Female subject, age 40–49; the photograph is a close-up of the affected area — 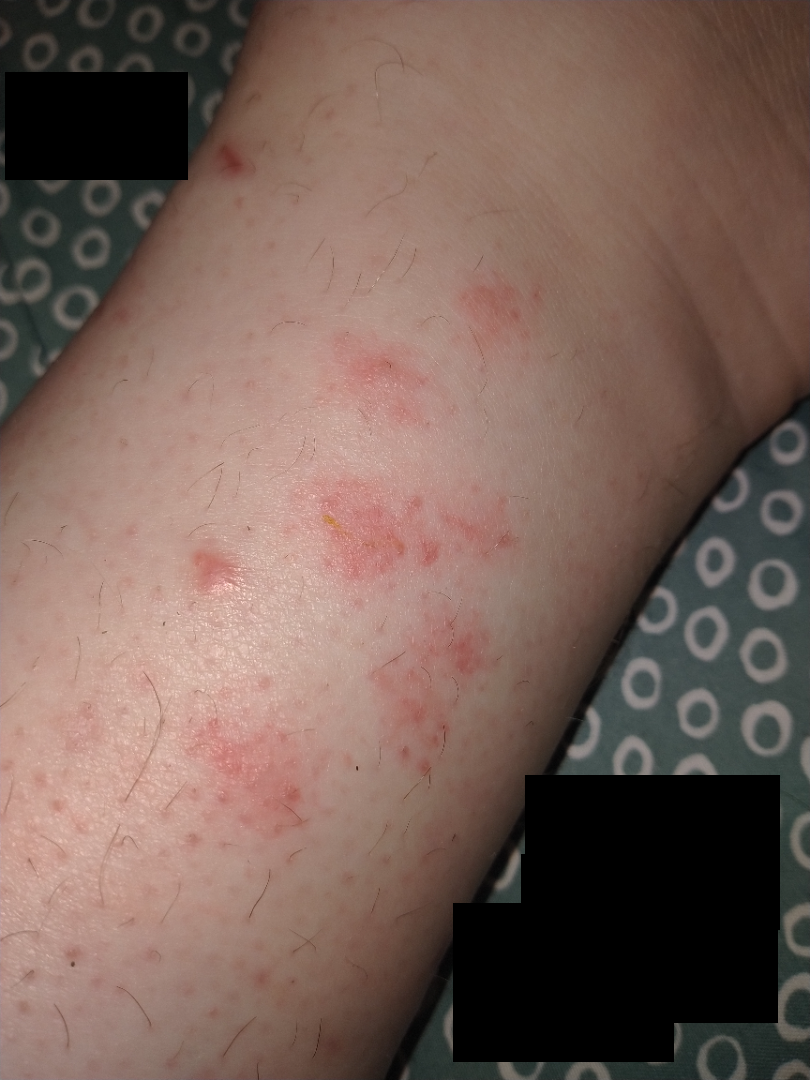The case was indeterminate on photographic review.